A dermoscopic photograph of a skin lesion.
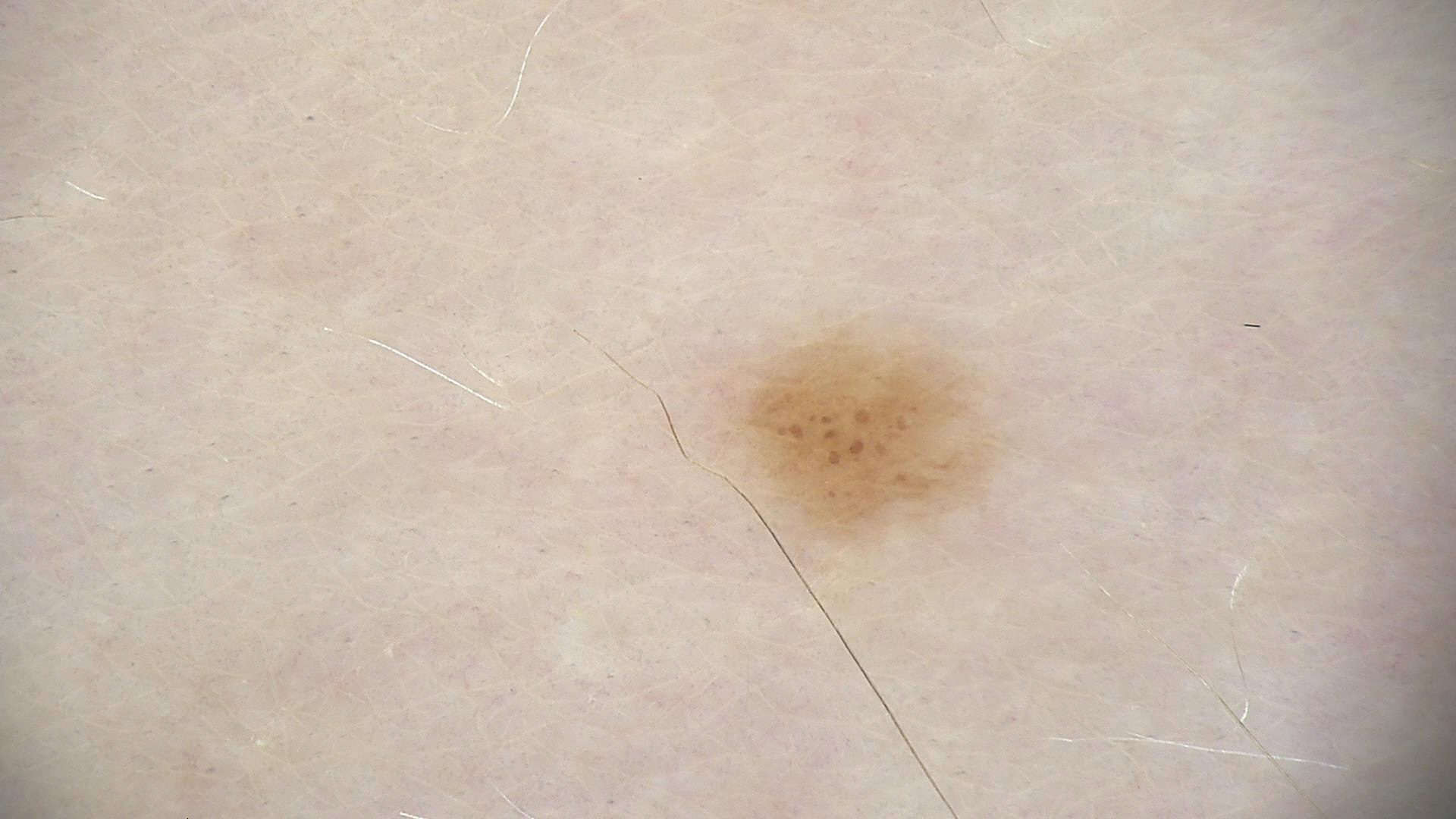{
  "diagnosis": {
    "name": "dysplastic junctional nevus",
    "code": "jd",
    "malignancy": "benign",
    "super_class": "melanocytic",
    "confirmation": "expert consensus"
  }
}